The photograph is a close-up of the affected area:
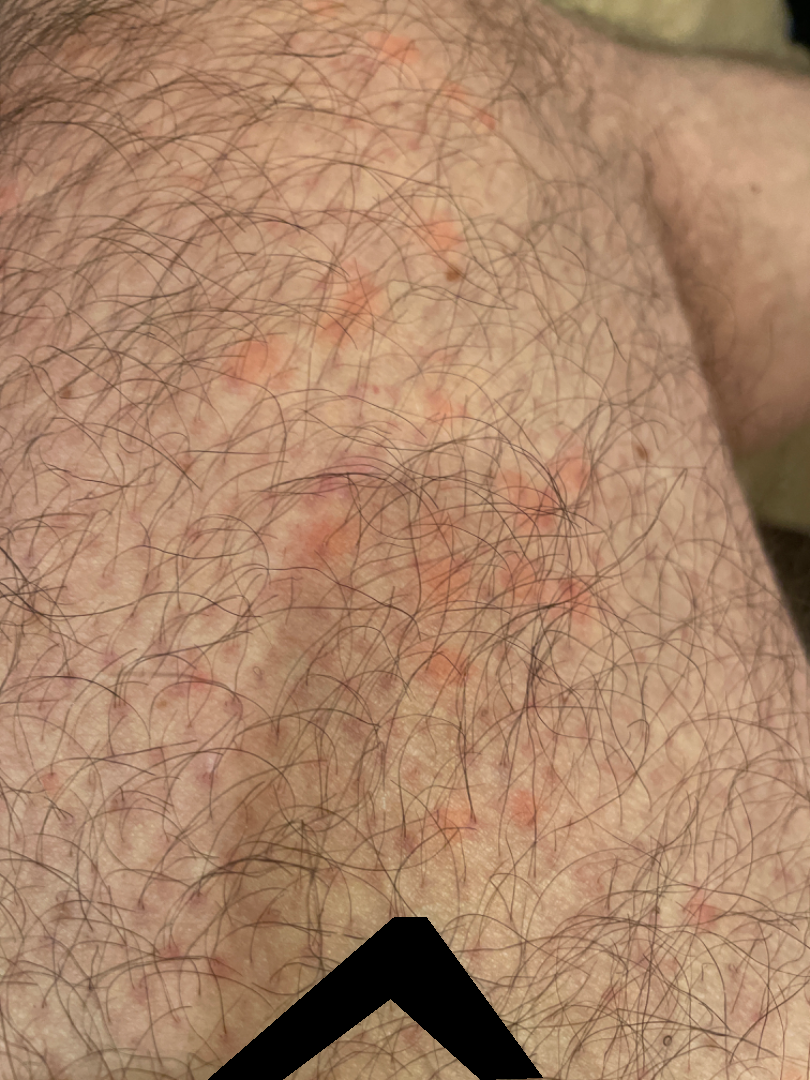{"assessment": "ungradable on photographic review"}